An image taken at an angle; female contributor, age 18–29 — 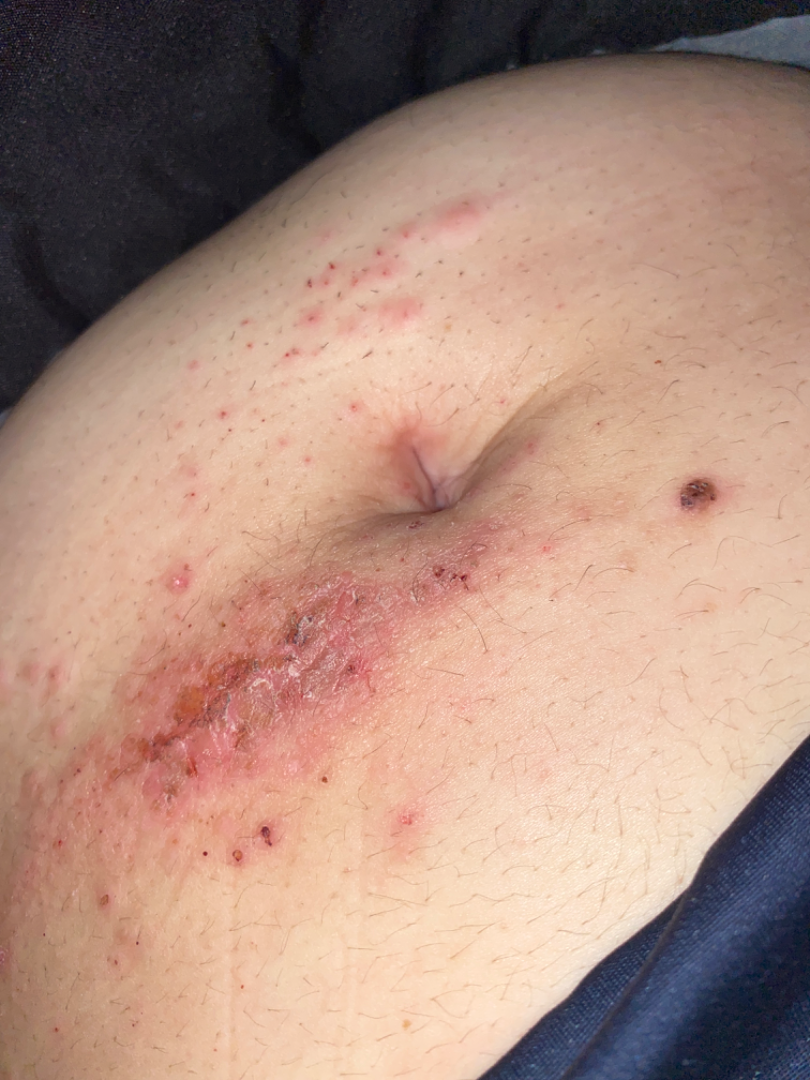Q: Patient's own categorization?
A: a rash
Q: When did this start?
A: one to four weeks
Q: Reported symptoms?
A: darkening, itching and bleeding
Q: Any systemic symptoms?
A: none reported
Q: What is the differential diagnosis?
A: reviewed remotely by one dermatologist: most likely Allergic Contact Dermatitis; the differential also includes Irritant Contact Dermatitis